Texture is reported as flat, the patient considered this skin that appeared healthy to them, the patient reports bothersome appearance, located on the leg, close-up view, present for about one day:
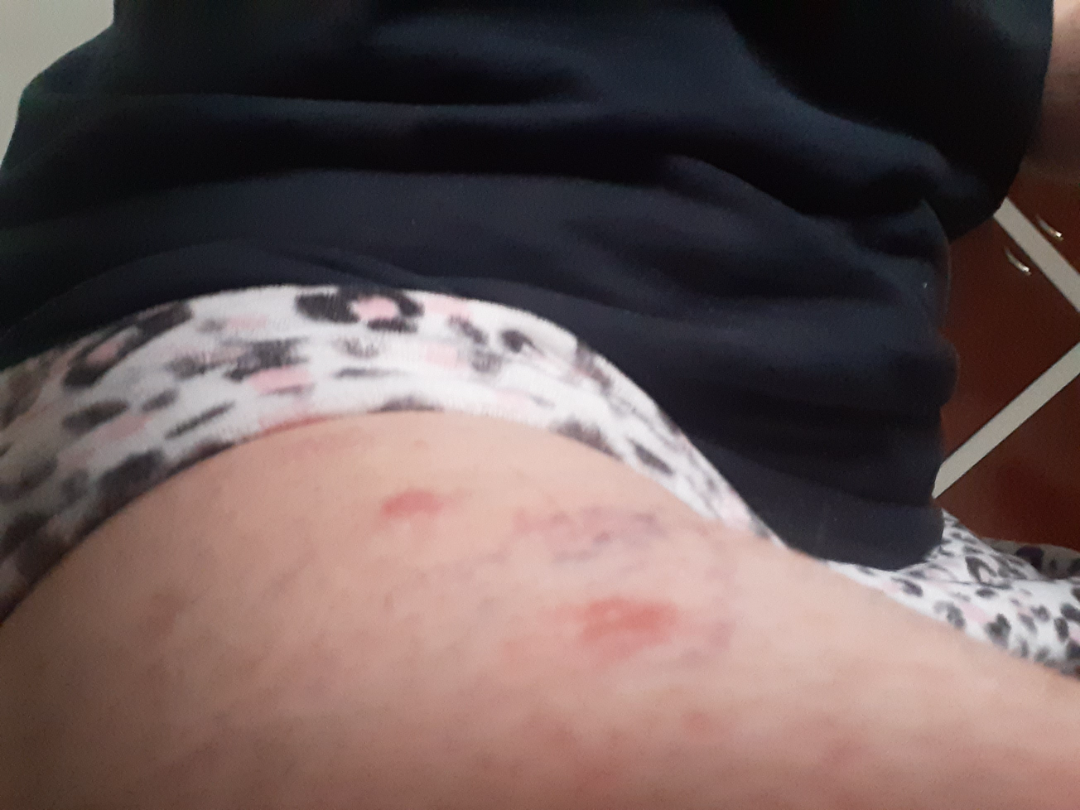assessment = ungradable on photographic review